A dermatoscopic image of a skin lesion: 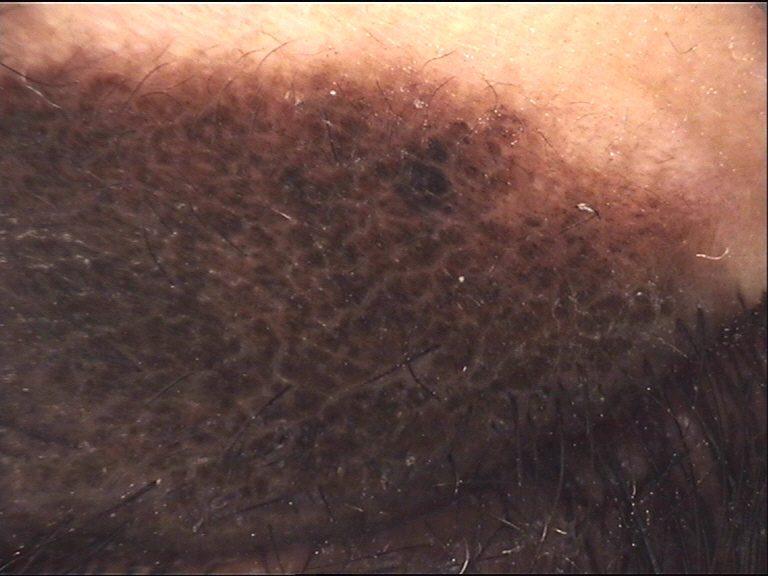  diagnosis:
    name: congenital compound nevus
    code: ccb
    malignancy: benign
    super_class: melanocytic
    confirmation: expert consensus